The patient is a female about 45 years old · this is a dermoscopic photograph of a skin lesion.
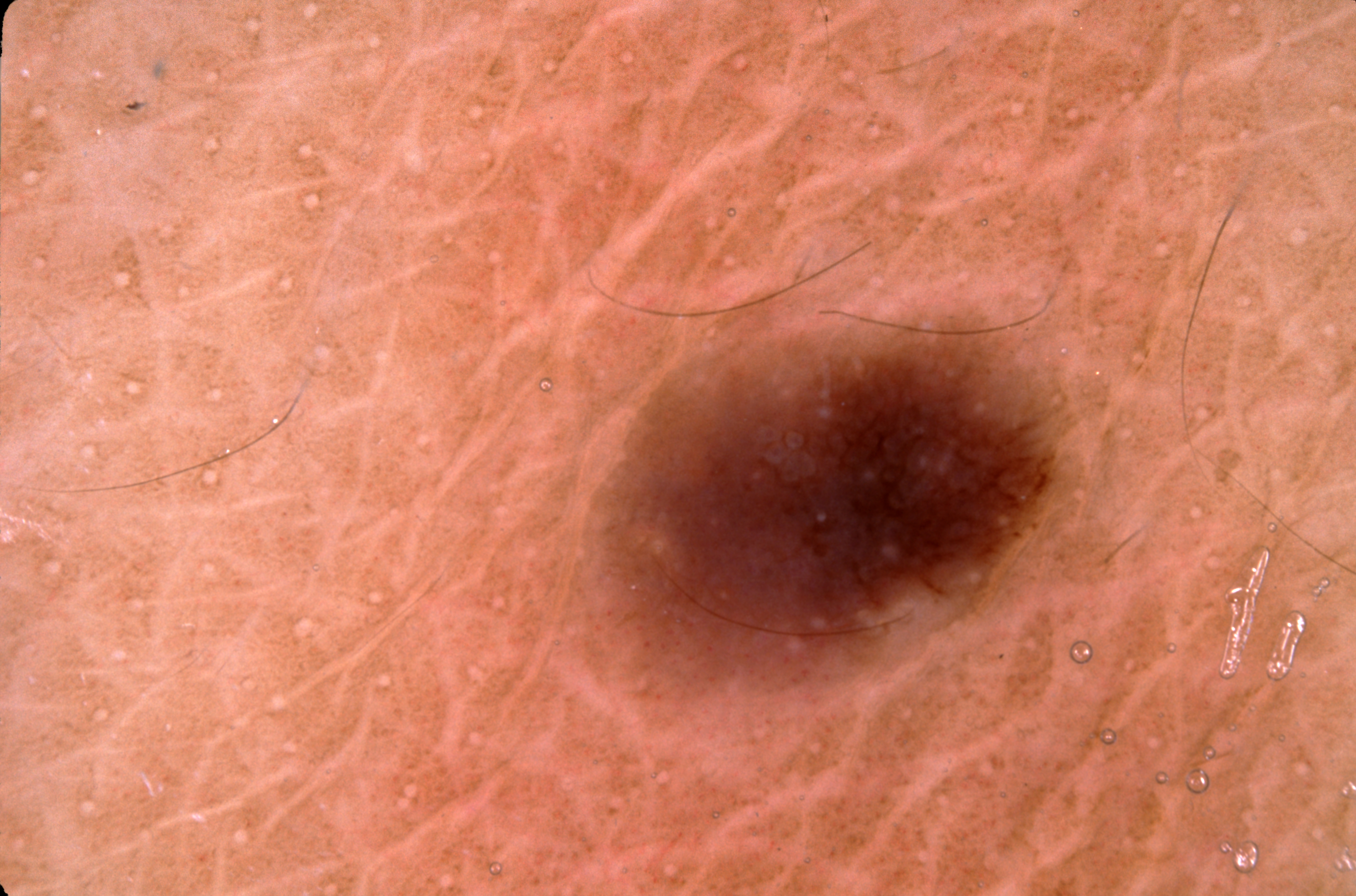Summary:
Dermoscopy demonstrates pigment network. With coordinates (x1, y1, x2, y2), lesion location: 604/322/1070/679.
Conclusion:
Consistent with a melanocytic nevus, a benign skin lesion.